Dermoscopy of a skin lesion. Imaged for a research study, with no referral diagnosis recorded. A female subject 59 years old: 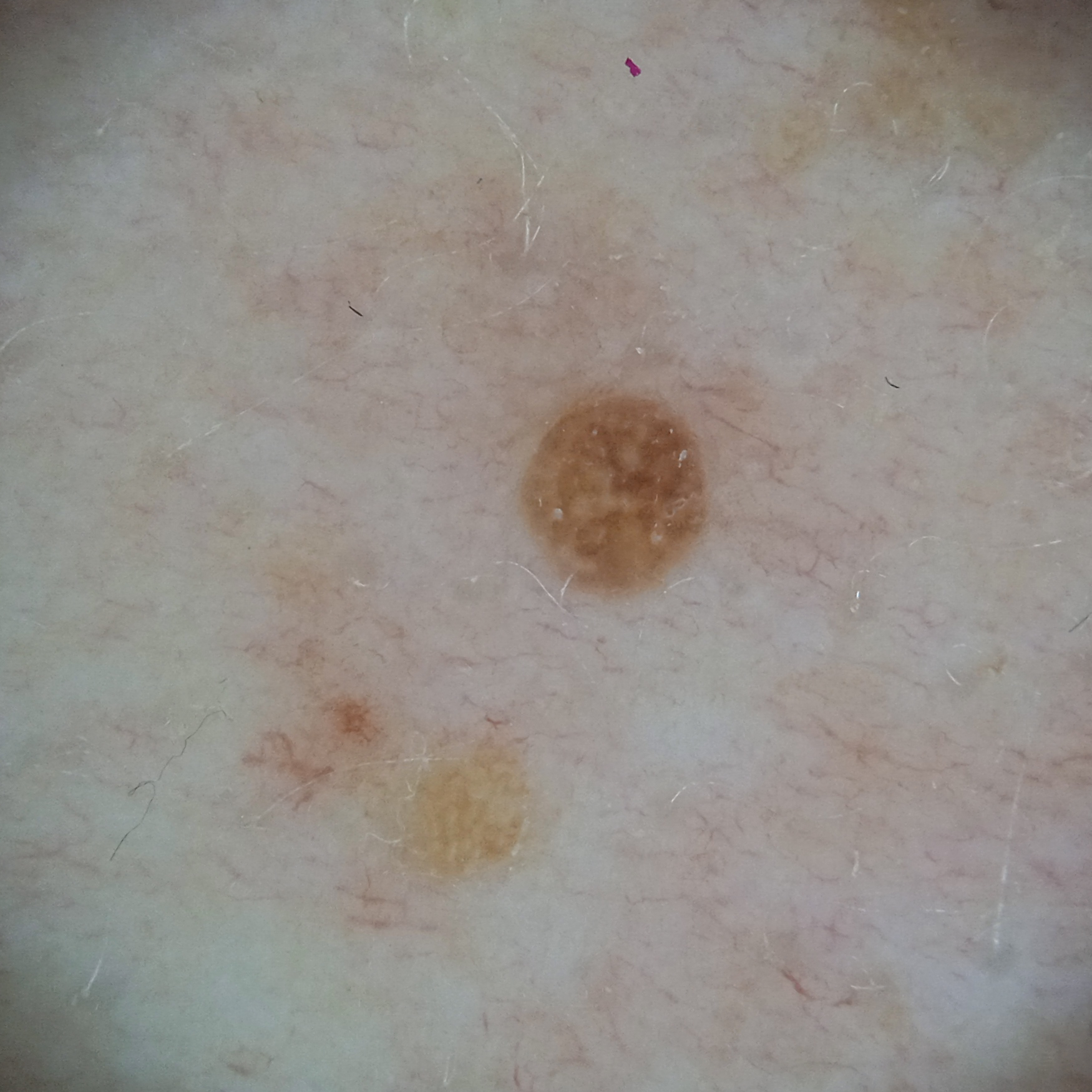Findings:
Located on the torso. Measuring roughly 2.2 mm.
Impression:
The consensus diagnosis for this lesion was a seborrheic keratosis.